This is a dermoscopic photograph of a skin lesion:
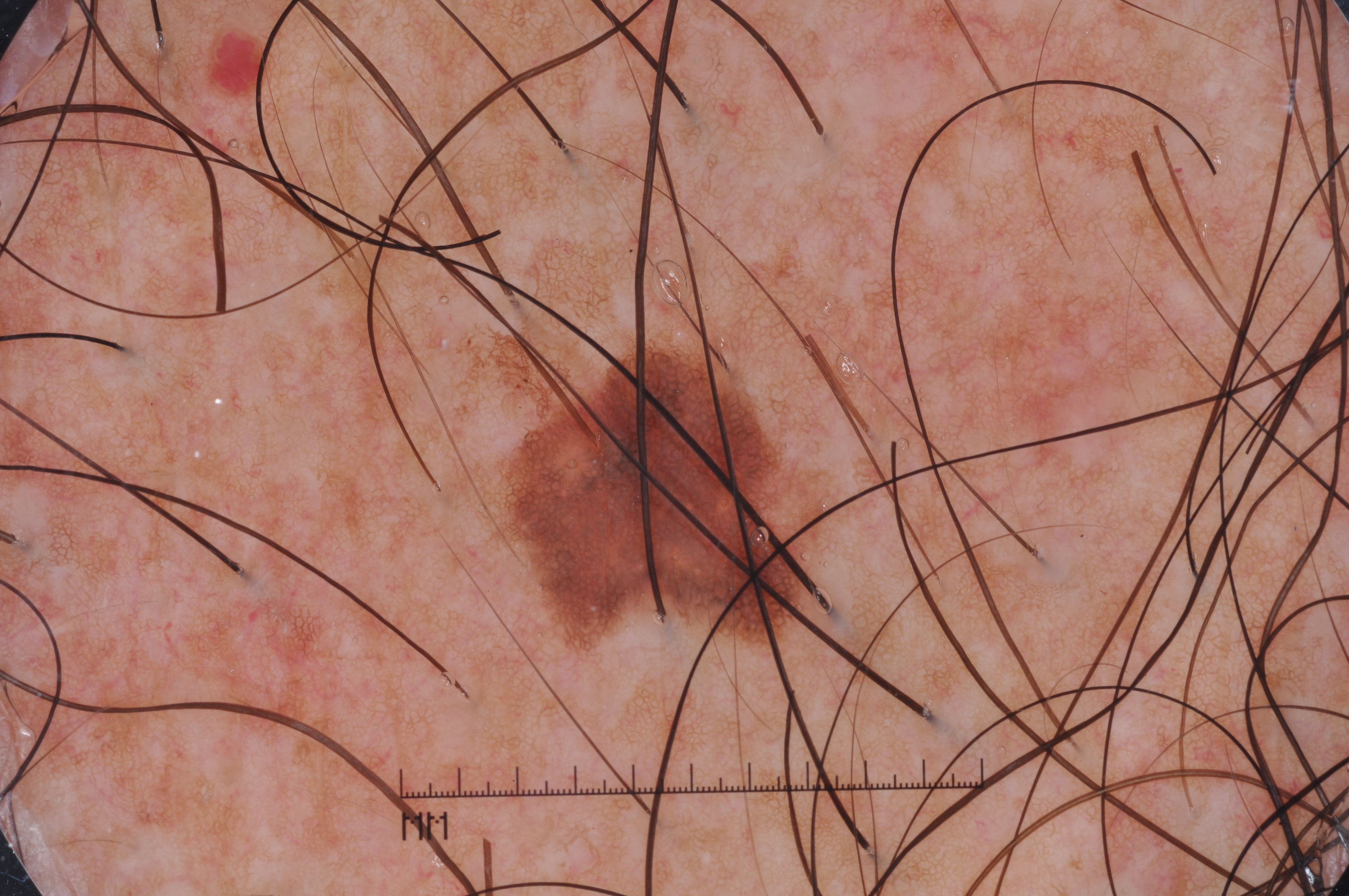The lesion's extent is box(506, 350, 801, 630).
The lesion takes up about 5% of the image.
Dermoscopy demonstrates pigment network.
Expert review diagnosed this as a melanocytic nevus, a benign lesion.